Dermoscopy of a skin lesion.
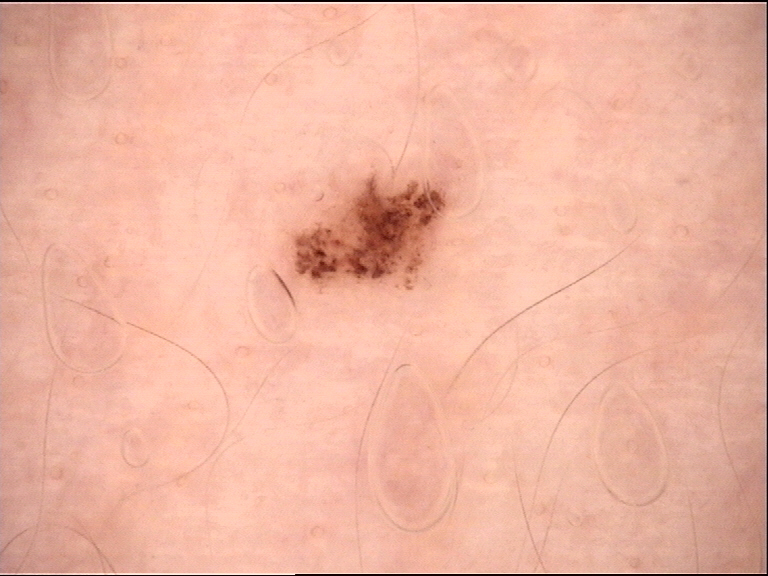Impression: Consistent with a dysplastic junctional nevus.